The arm is involved. The patient reported no systemic symptoms. No associated lesion symptoms were reported. The contributor is male. The lesion is described as flat. The photograph is a close-up of the affected area:
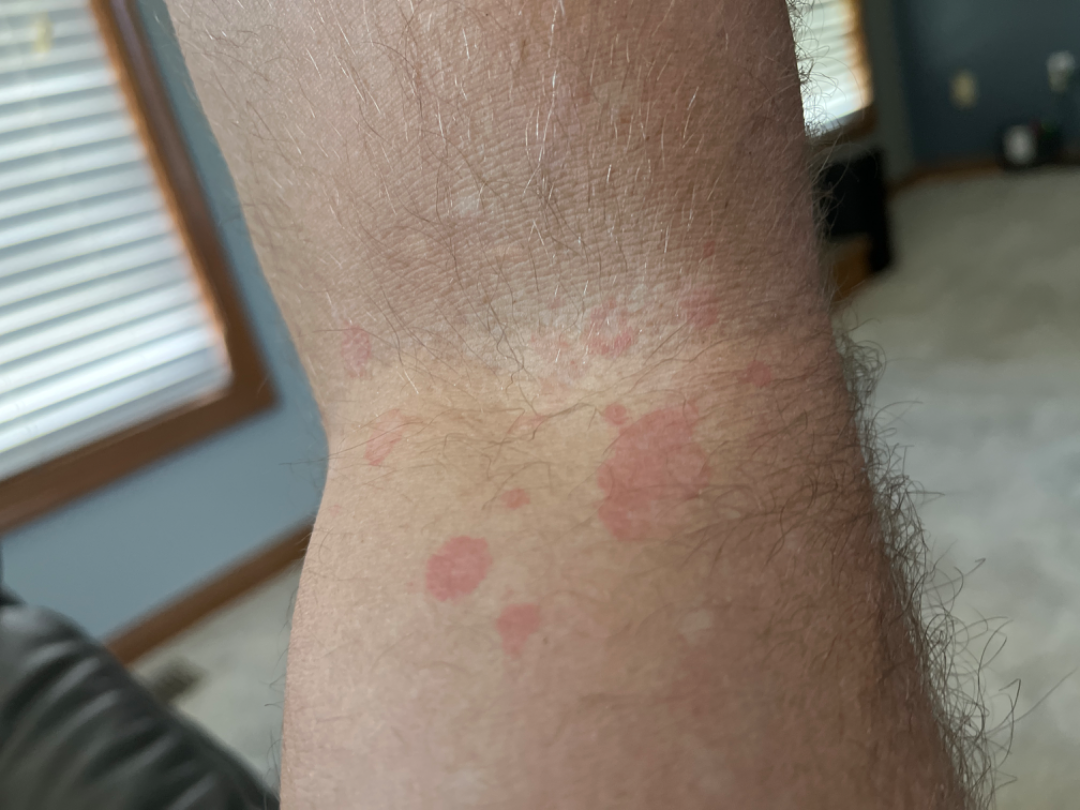Review: The reviewing dermatologist was unable to assign a differential diagnosis from the image.